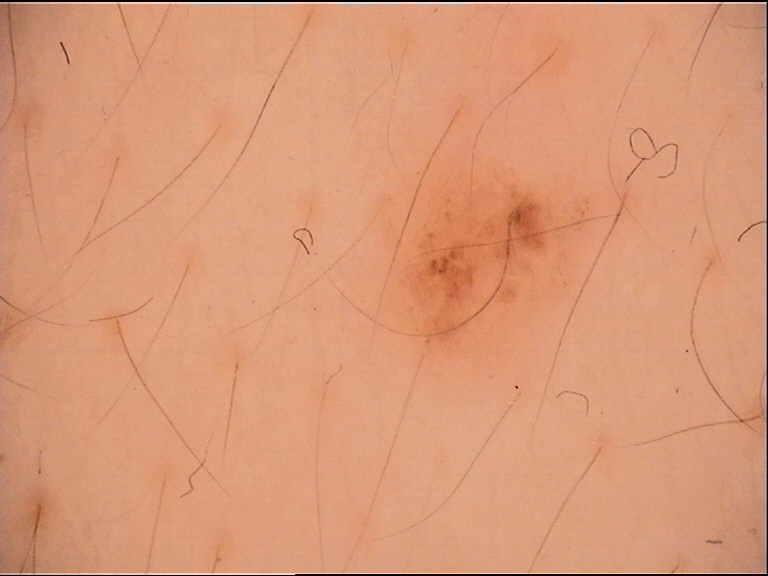Diagnosed as a banal lesion — a compound nevus.